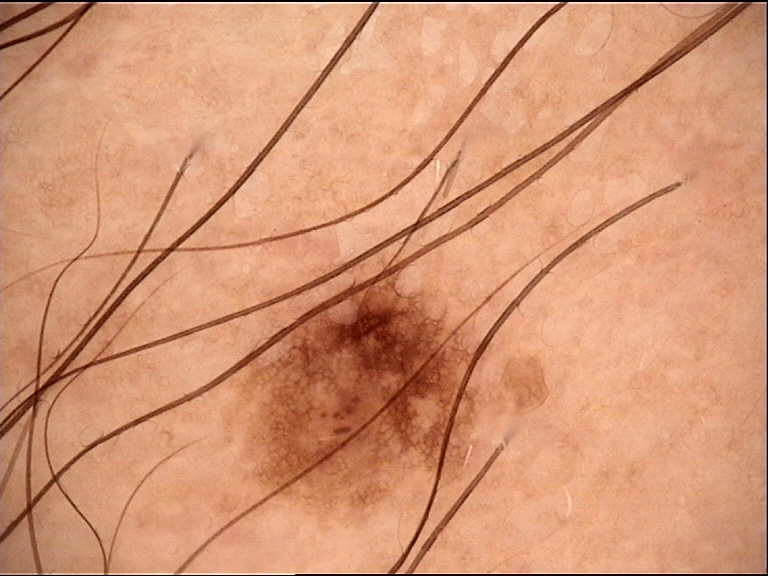Dermoscopy of a skin lesion. Consistent with a benign lesion — a dysplastic junctional nevus.